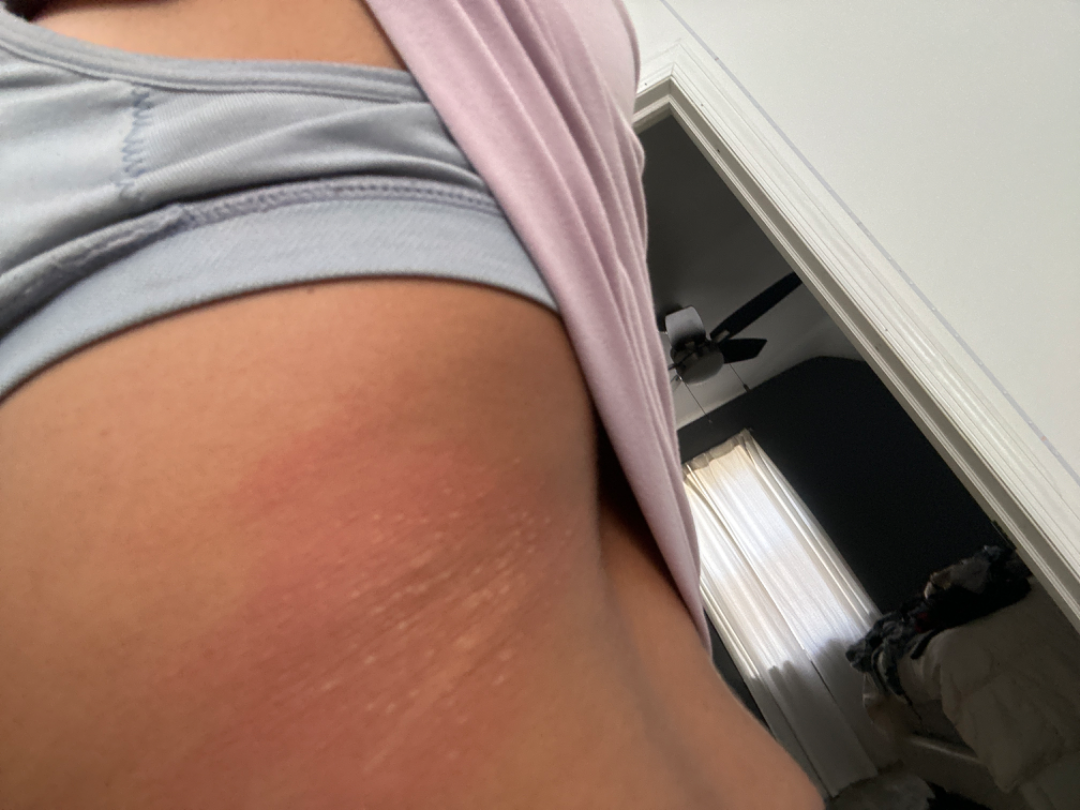Q: What was the assessment?
A: not assessable
Q: Patient's own categorization?
A: skin that appeared healthy to them
Q: Any systemic symptoms?
A: none reported
Q: How was the photo taken?
A: close-up
Q: How does the lesion feel?
A: raised or bumpy
Q: What symptoms does the patient report?
A: itching
Q: Fitzpatrick or Monk tone?
A: FST IV
Q: When did this start?
A: about one day